Dermoscopy of a skin lesion.
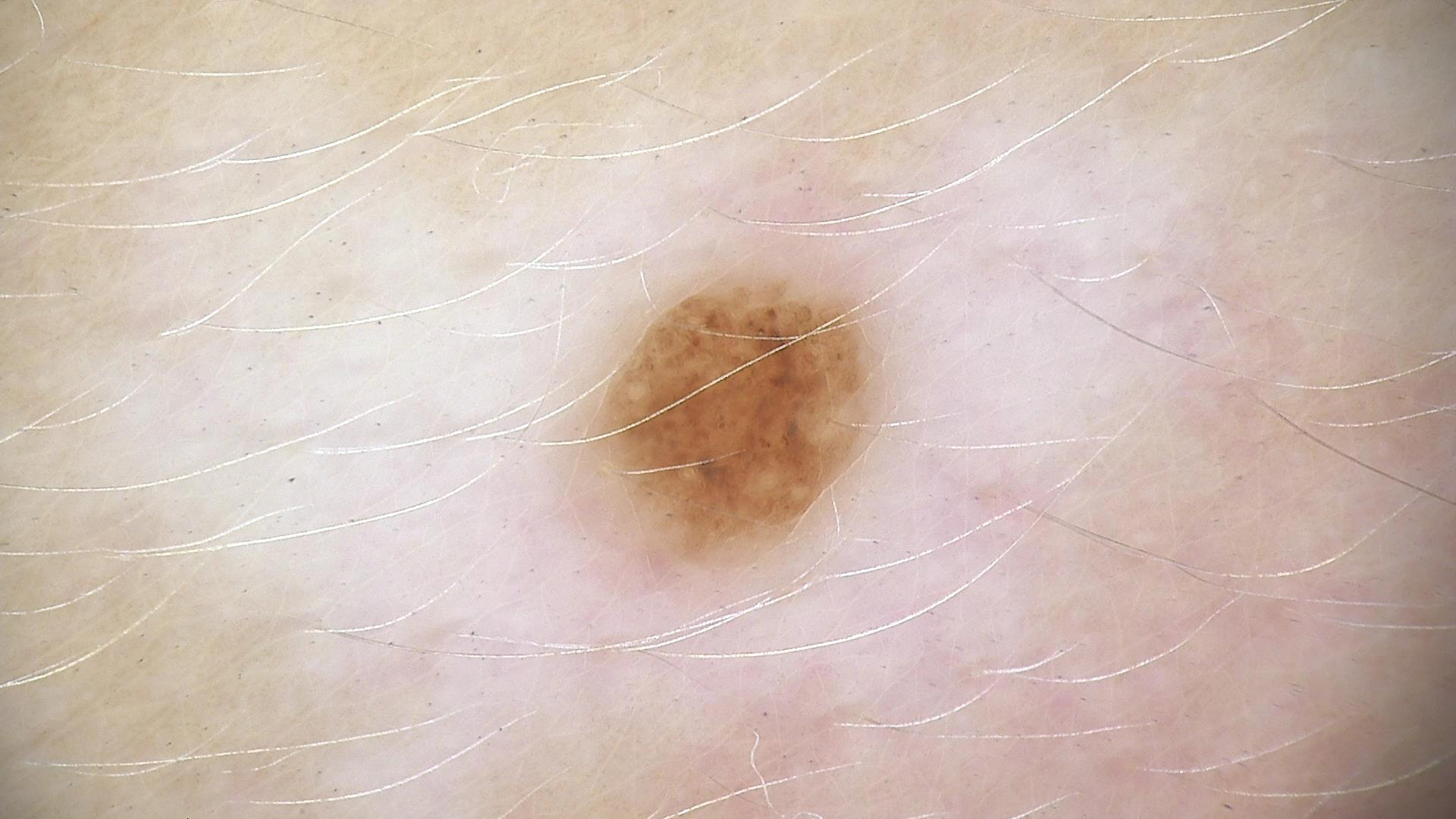Classified as a banal lesion — a compound nevus.